The contributor is 30–39, male · the photograph is a close-up of the affected area · reported duration is less than one week · texture is reported as raised or bumpy · located on the leg · the patient indicates itching and enlargement: 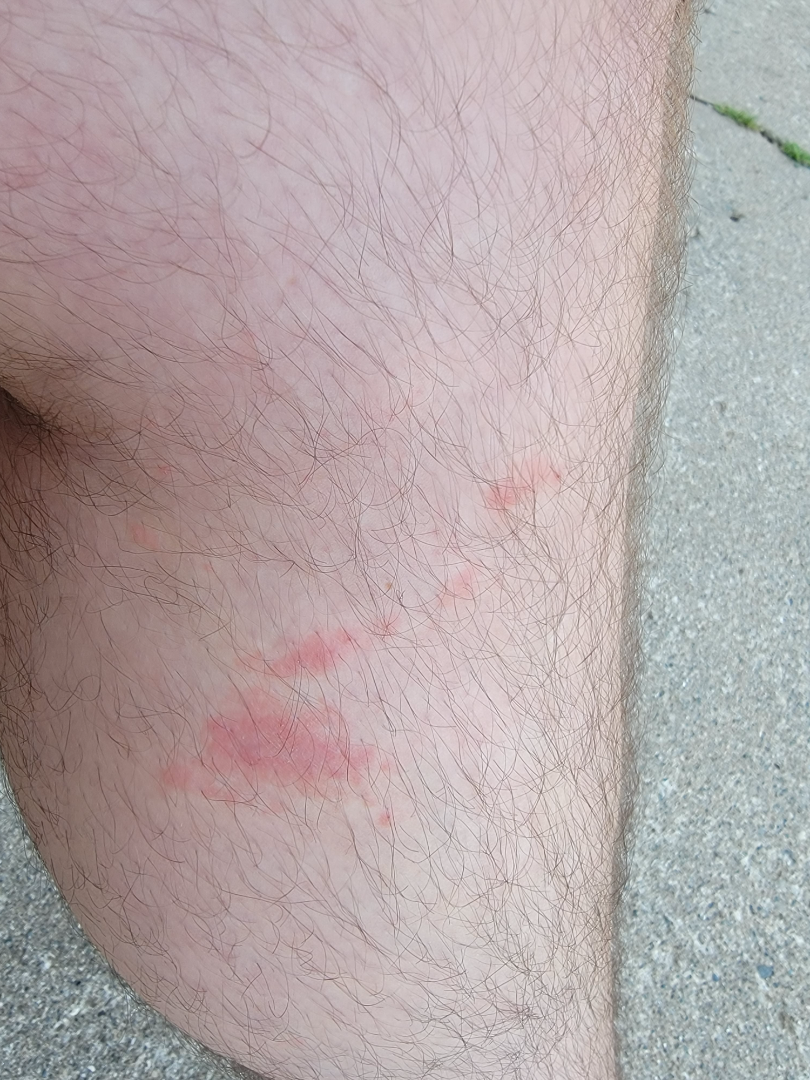The skin condition could not be confidently assessed from this image.